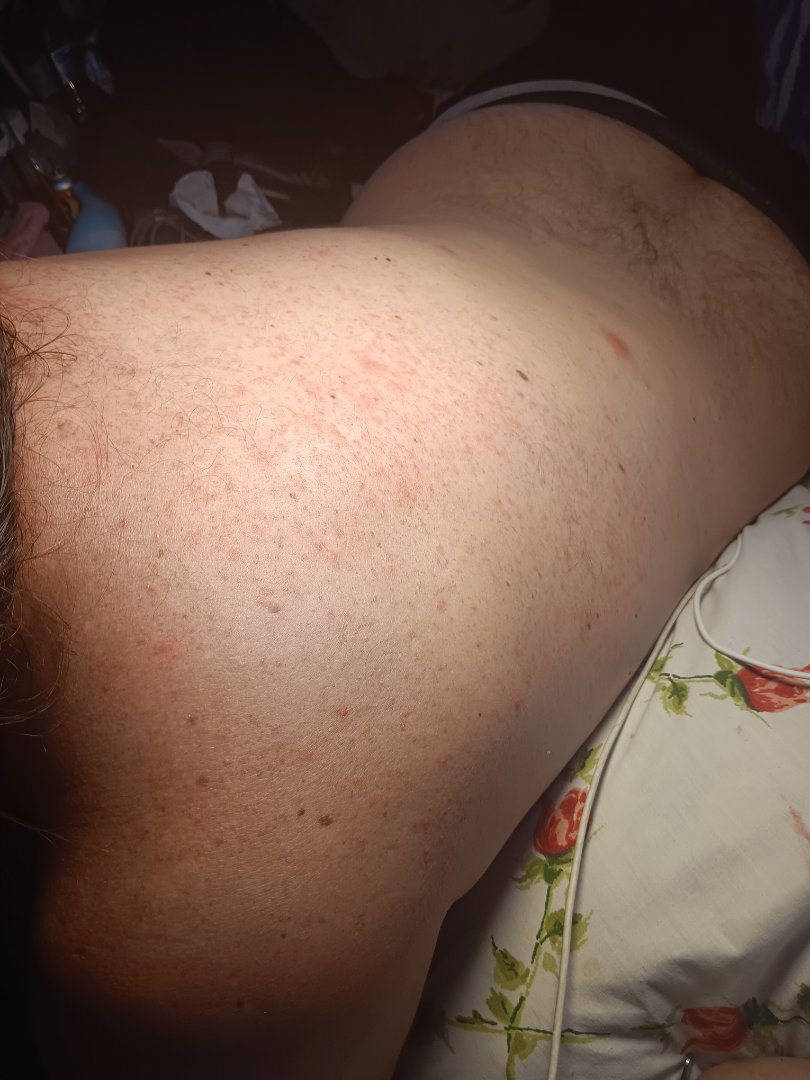Assessment: The reviewing dermatologist's impression was: Acute dermatitis, NOS (weight 1.00).